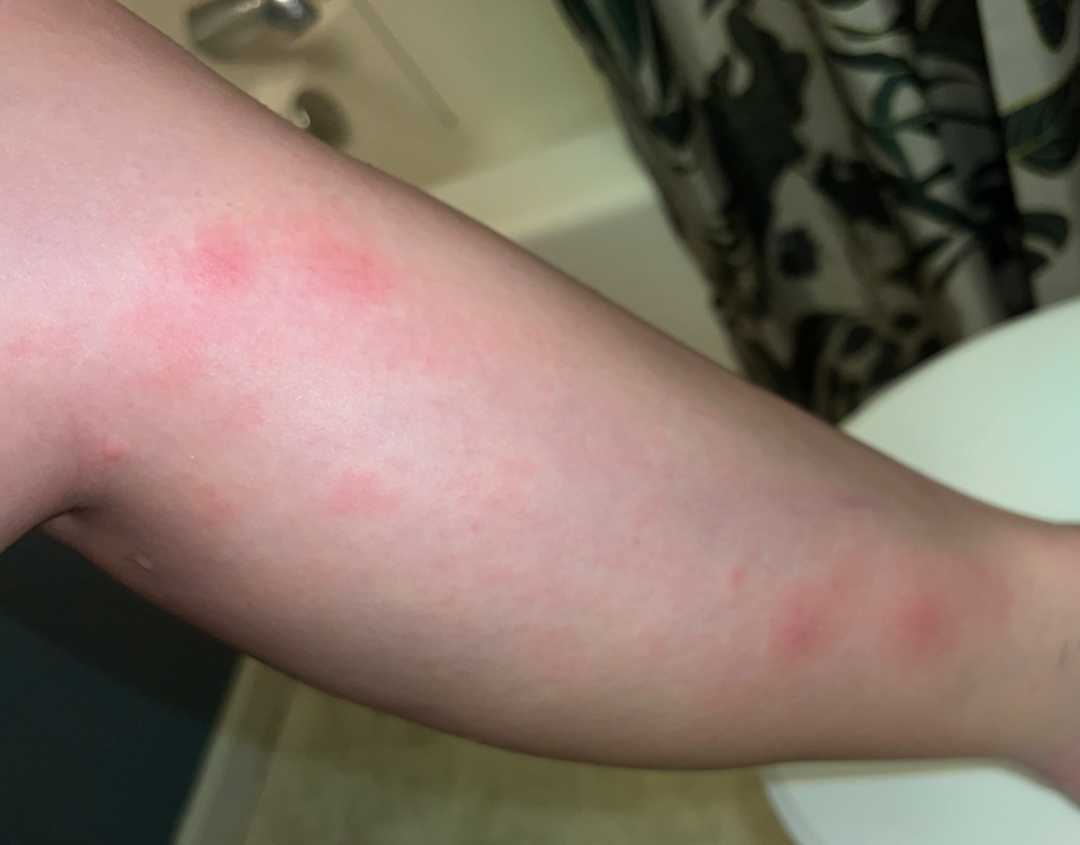This is a close-up image.
Located on the leg.
Reported lesion symptoms include pain, itching and bothersome appearance.
The patient notes the lesion is rough or flaky.
Self-categorized by the patient as a rash.
Reported duration is one to four weeks.
Favoring Urticaria; possibly Insect Bite.